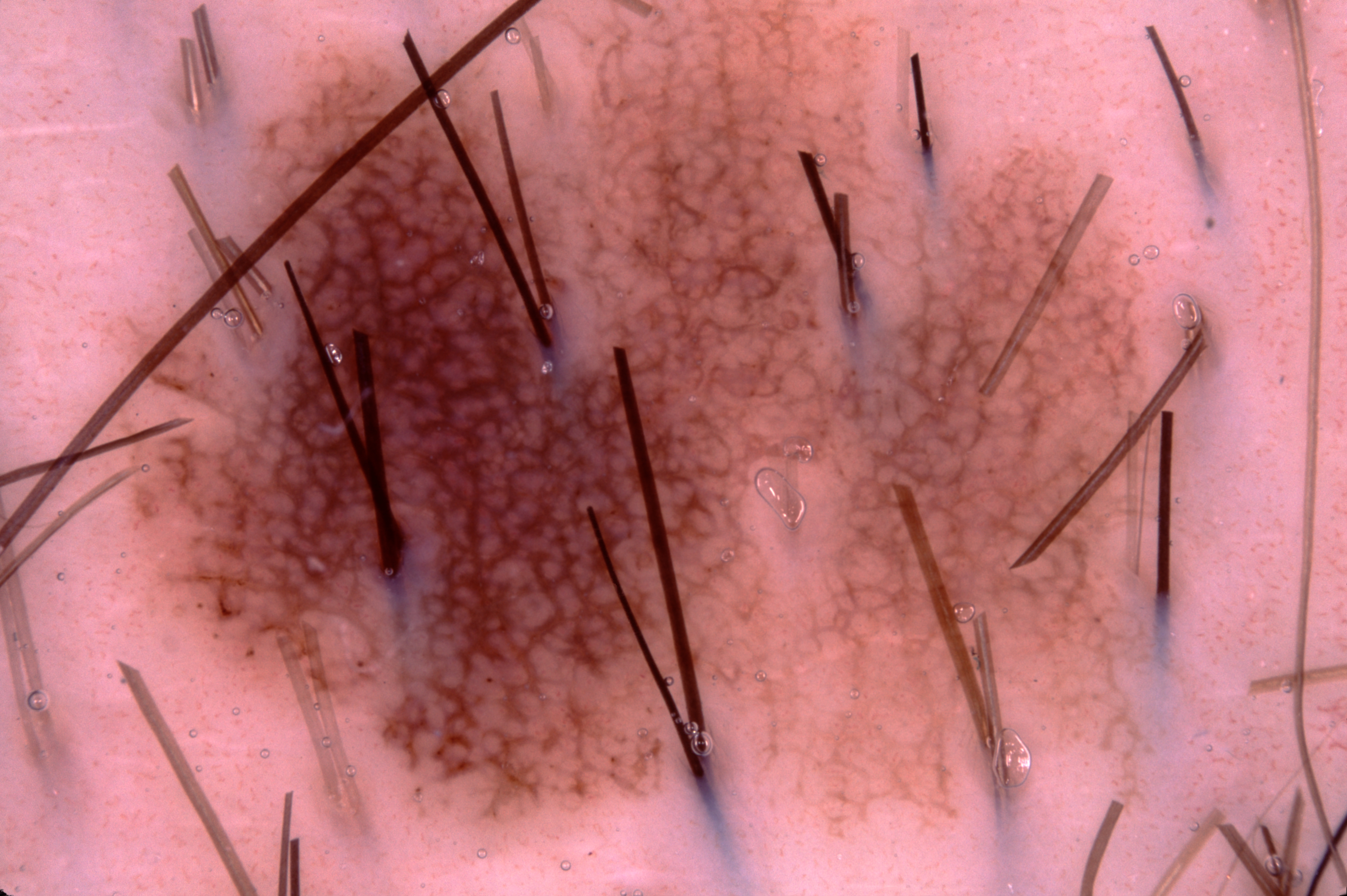Summary:
A male patient in their mid-20s. A dermoscopic view of a skin lesion. Dermoscopic assessment notes pigment network, with no milia-like cysts, streaks, or negative network. The visible lesion spans left=85, top=0, right=1221, bottom=826.
Conclusion:
Diagnosed as a melanocytic nevus.